Fitzpatrick IV; an image taken at an angle; the contributor is 40–49, female; texture is reported as rough or flaky; the patient reports enlargement; the affected area is the leg; the condition has been present for one to three months:
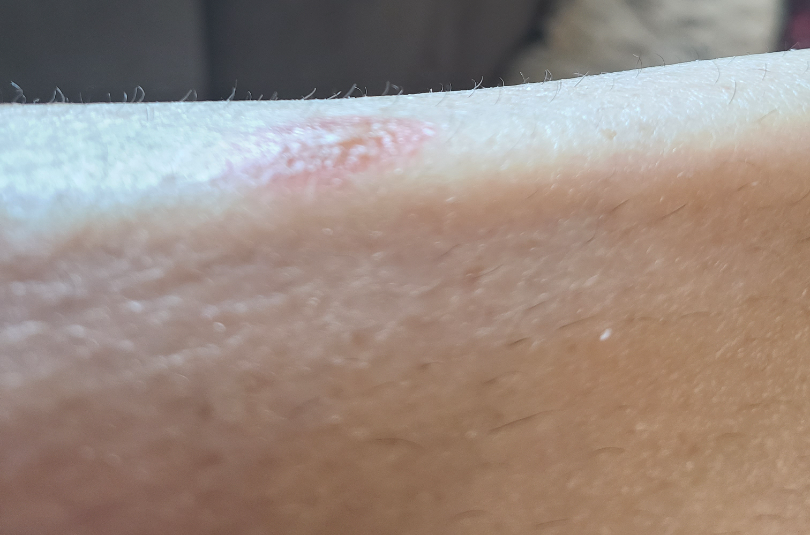The reviewer was unable to grade this case for skin condition.